Acquired for a research image collection, with no referral diagnosis. A dermoscopy image of a skin lesion. Few moles overall by the patient's own estimate. The patient says their skin reddens with sun exposure.
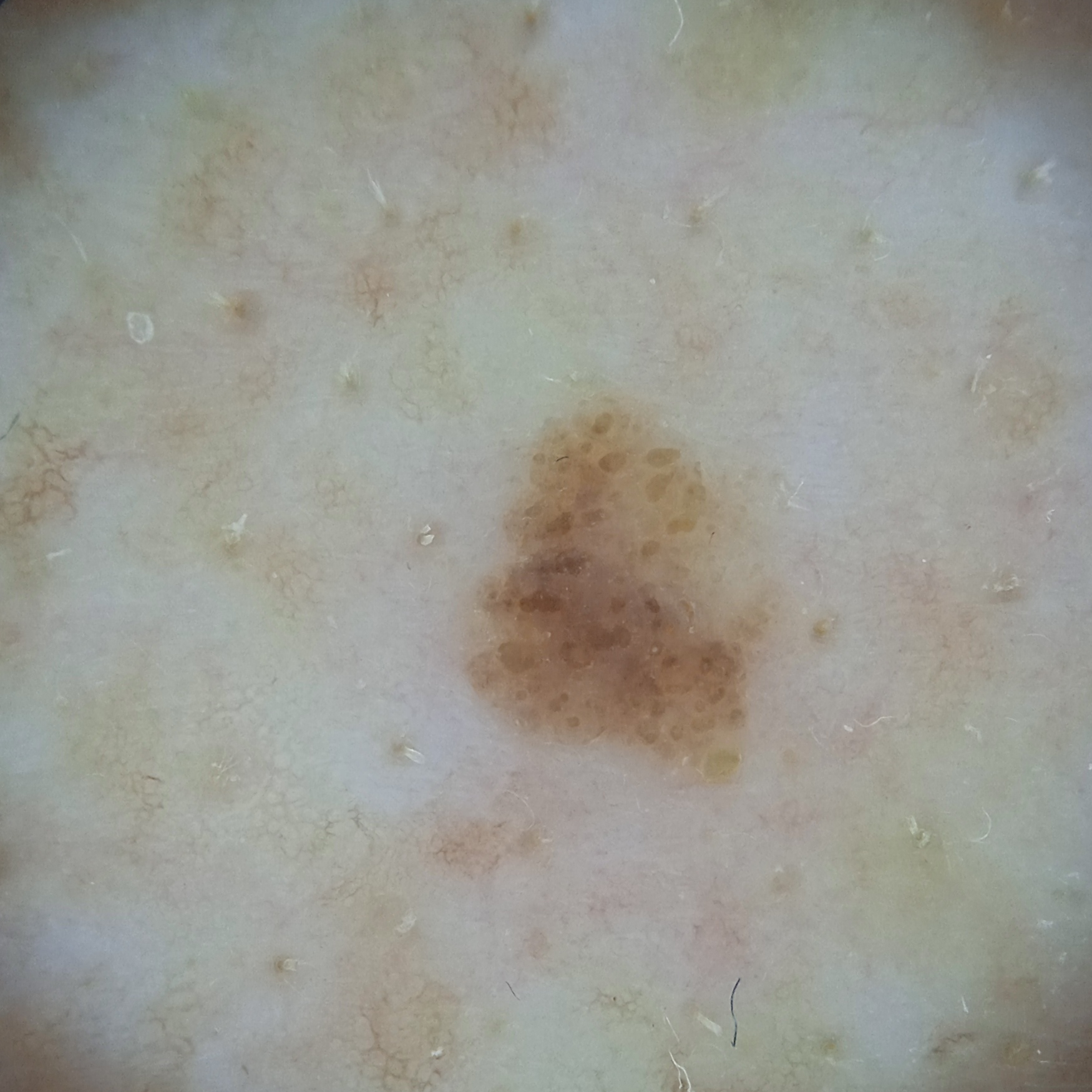The lesion is located on the back.
The lesion measures approximately 4.5 mm.
Four dermatologists reviewed the lesion; the consensus was a seborrheic keratosis; the reviewers were not unanimous.